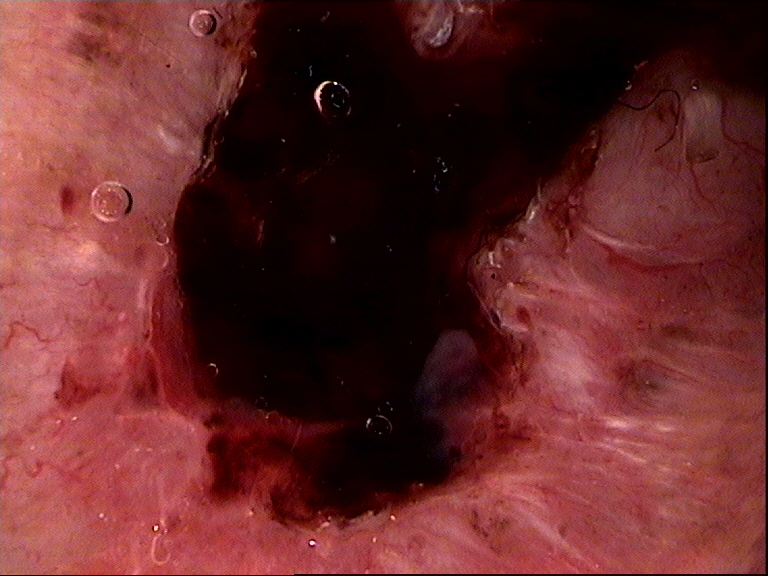Biopsy-confirmed as a basal cell carcinoma.